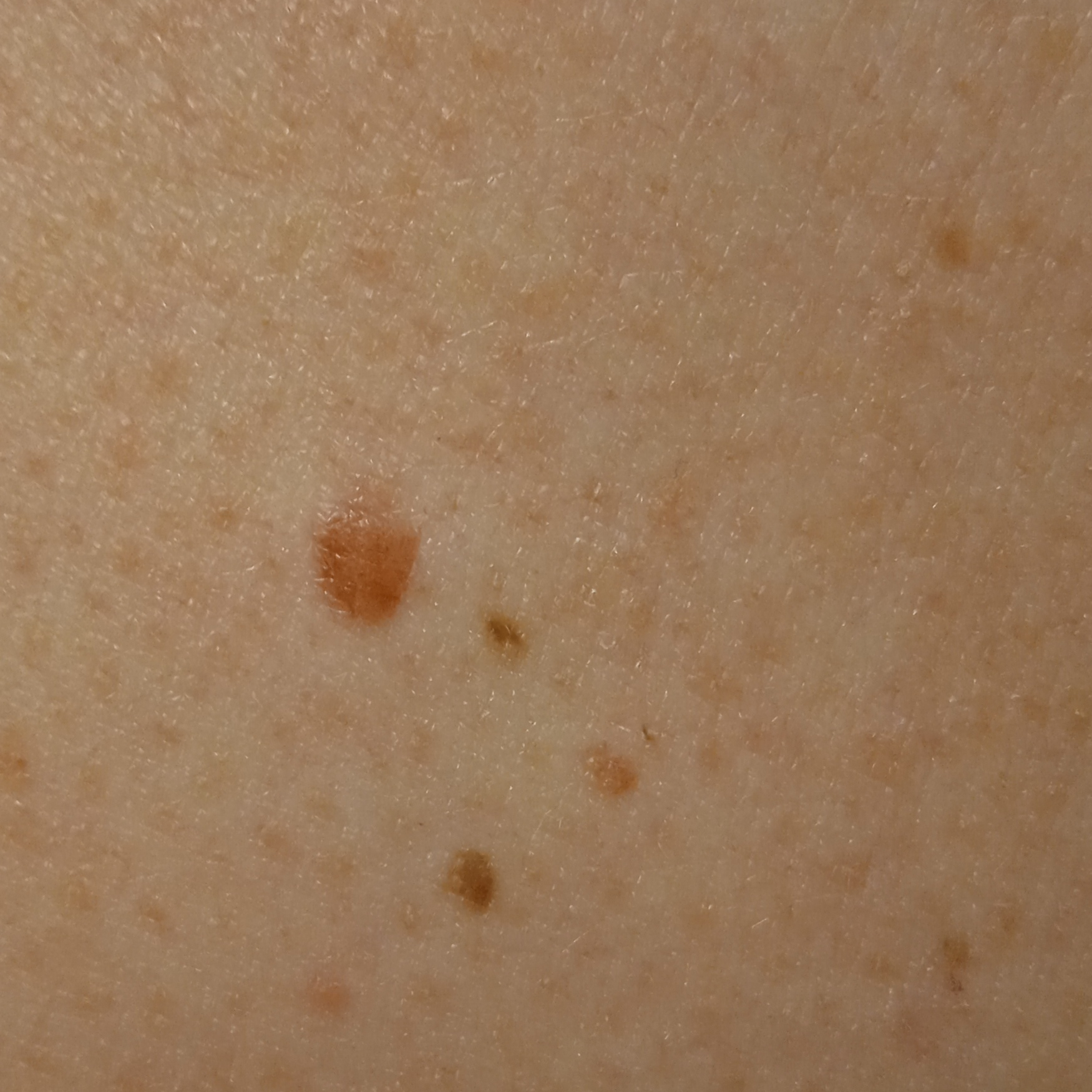A male patient 65 years of age. The patient says their skin reddens painfully with sun exposure. By self-report, a personal history of skin cancer, immunosuppression, and a family history of skin cancer. The lesion is about 4.4 mm across. The consensus diagnosis for this lesion was a melanocytic nevus.